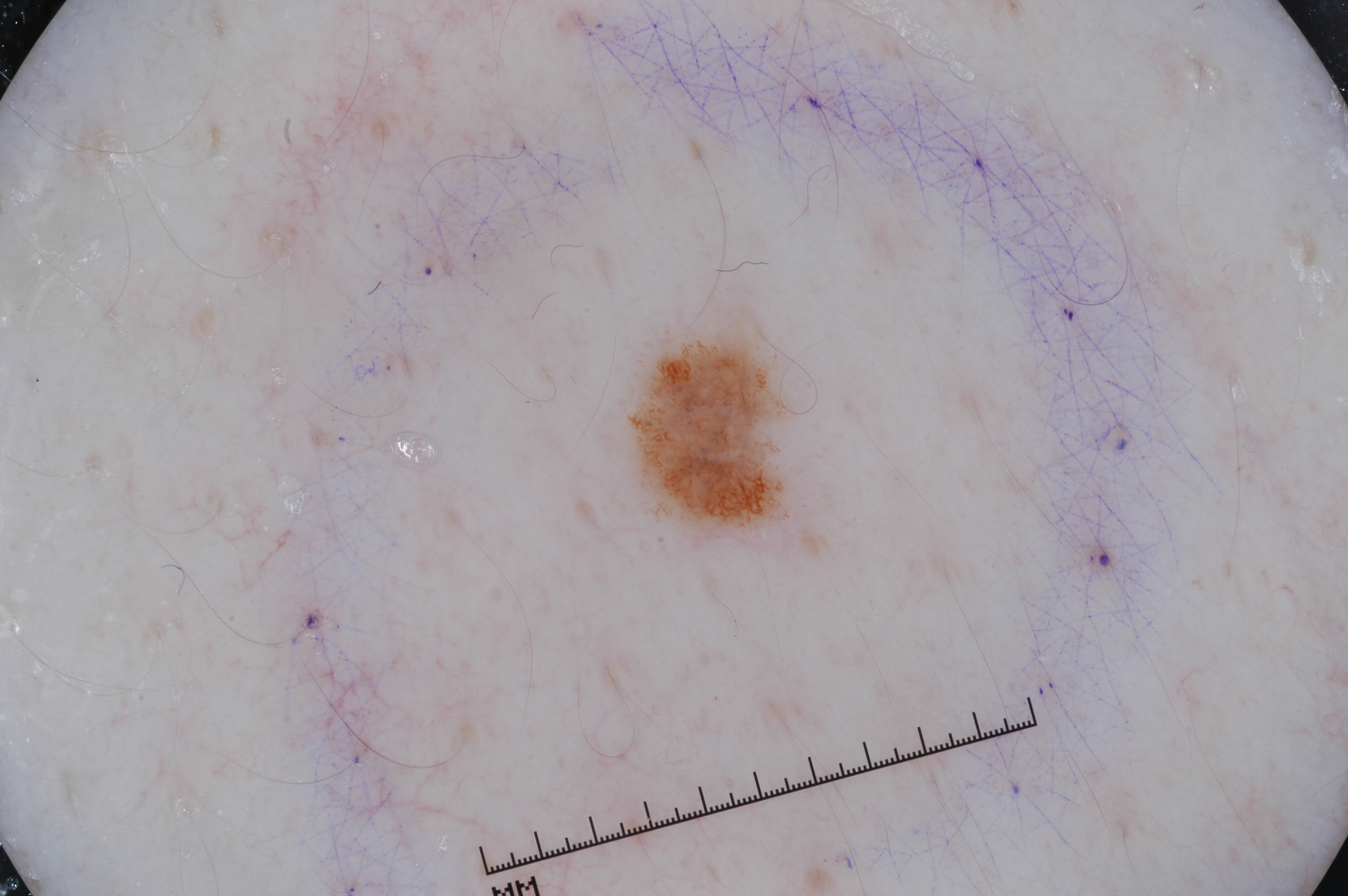Q: Who is the patient?
A: male, approximately 30 years of age
Q: What kind of image is this?
A: dermatoscopic image of a skin lesion
Q: How much of the field does the lesion occupy?
A: small
Q: Which dermoscopic features were noted?
A: pigment network; absent: milia-like cysts, negative network, and streaks
Q: What is the lesion's bounding box?
A: <box>624, 321, 802, 542</box>
Q: What is this lesion?
A: a melanocytic nevus